The photograph was taken at an angle. Located on the front of the torso and back of the torso. The patient also reports fatigue. The contributor reports itching. The patient is 40–49, female. Fitzpatrick II. The contributor reports the condition has been present for less than one week. The contributor reports the lesion is fluid-filled and raised or bumpy — 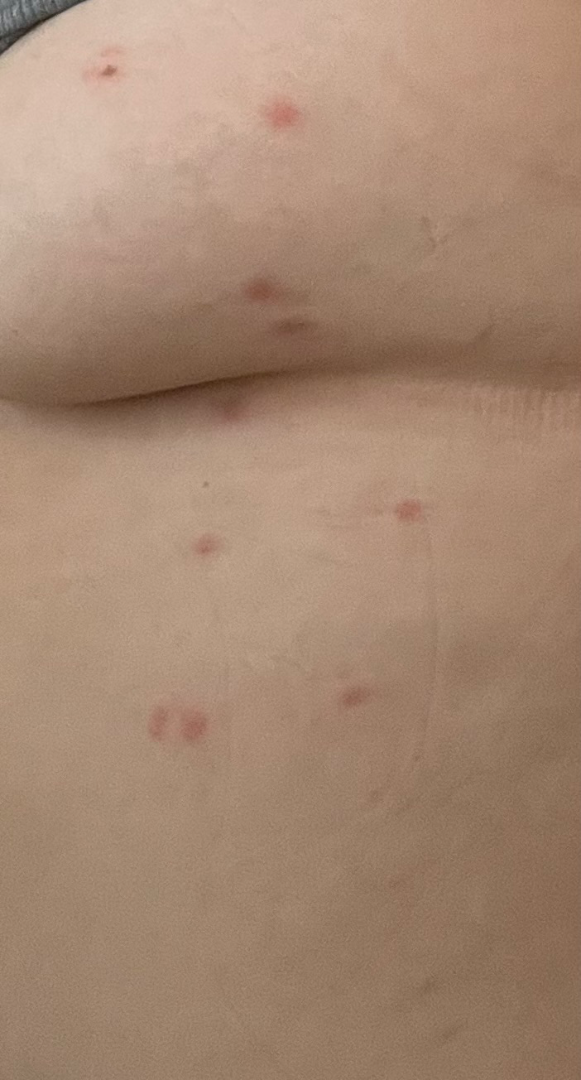diagnostic considerations=reviewed remotely by three dermatologists: the differential is split between Folliculitis and Insect Bite; less probable is Cyst.